Dermoscopy of a skin lesion: 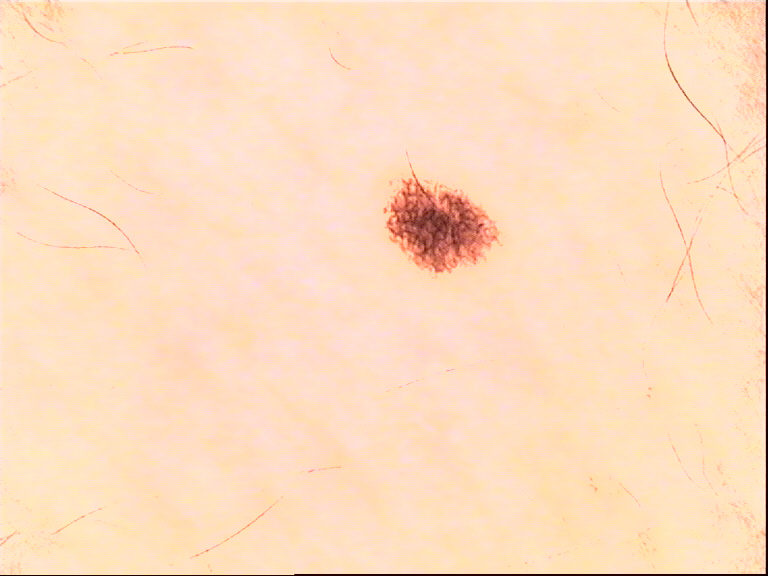class: dysplastic junctional nevus (expert consensus).